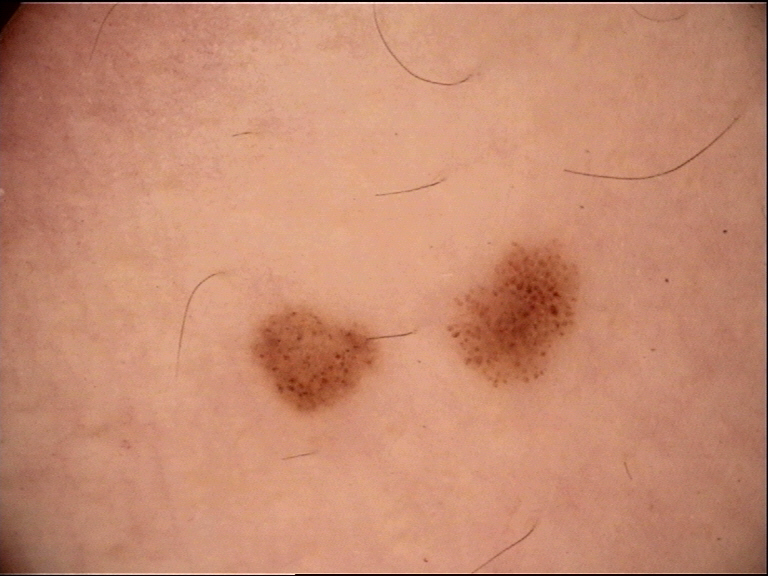Classified as a dysplastic junctional nevus.